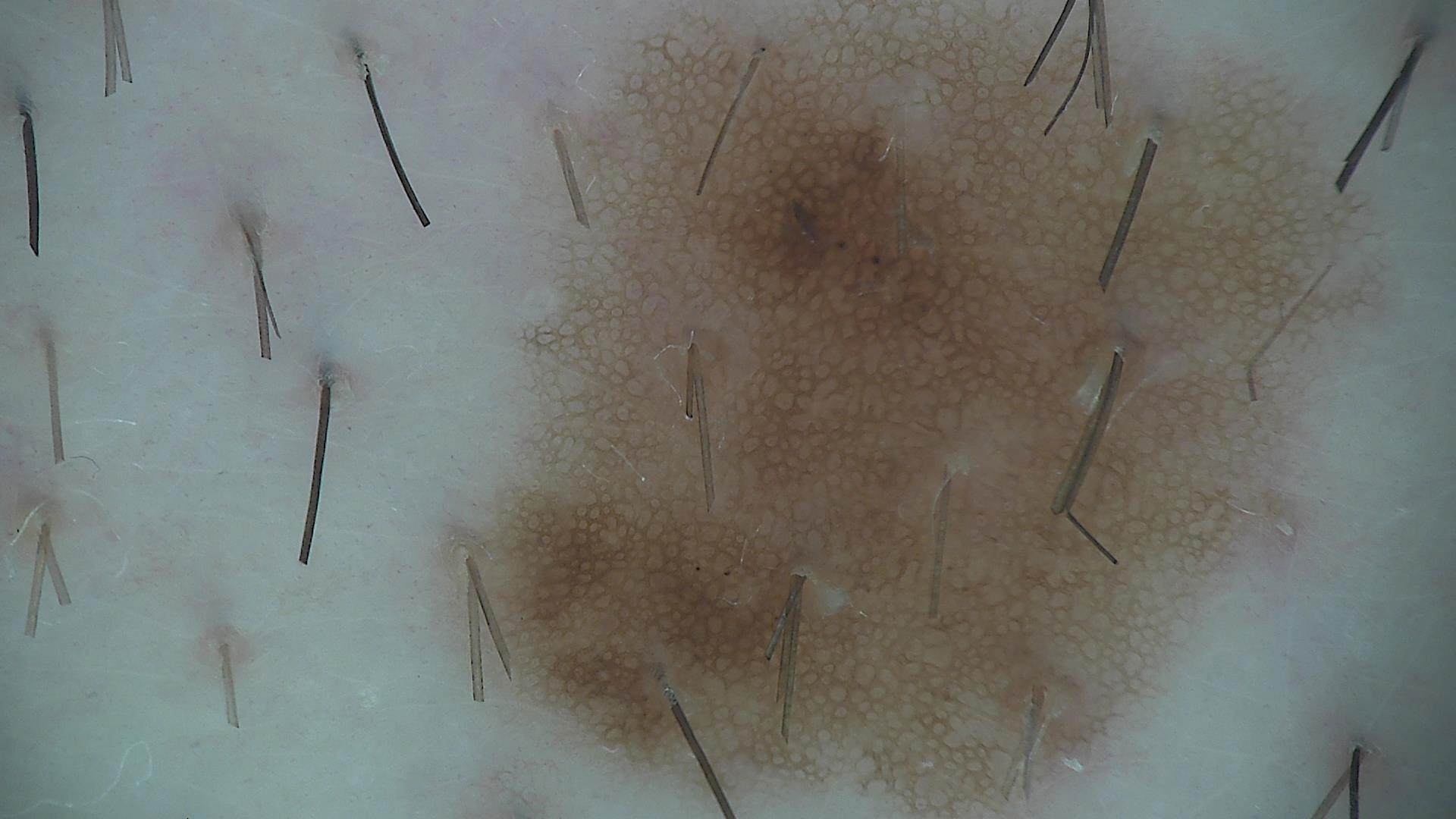{
  "diagnosis": {
    "name": "dysplastic junctional nevus",
    "code": "jd",
    "malignancy": "benign",
    "super_class": "melanocytic",
    "confirmation": "expert consensus"
  }
}